Contact-polarized dermoscopy of a skin lesion; a female subject aged 73-77 — 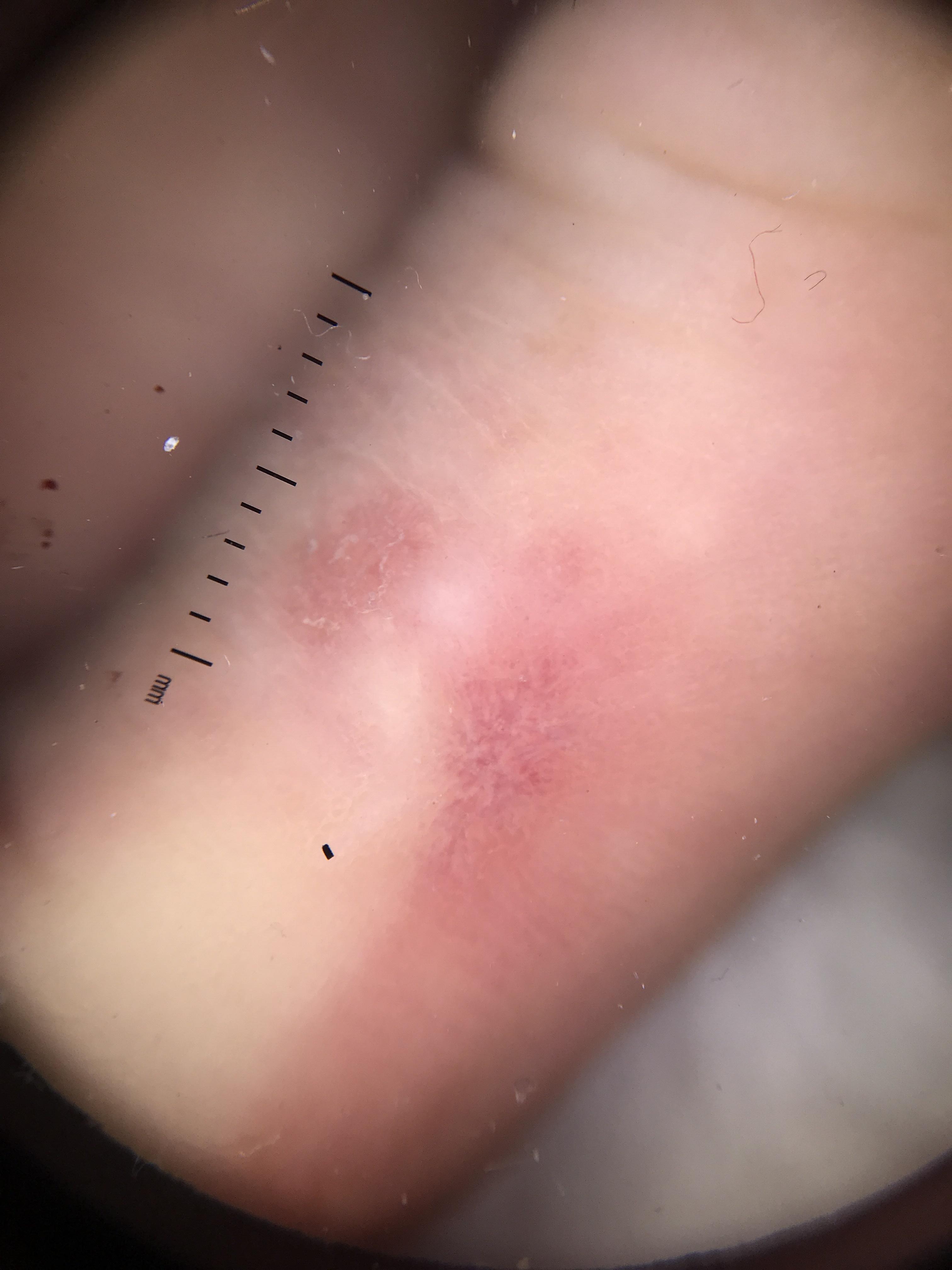Biopsy-confirmed as a squamous cell carcinoma.